A clinical close-up photograph of a skin lesion — 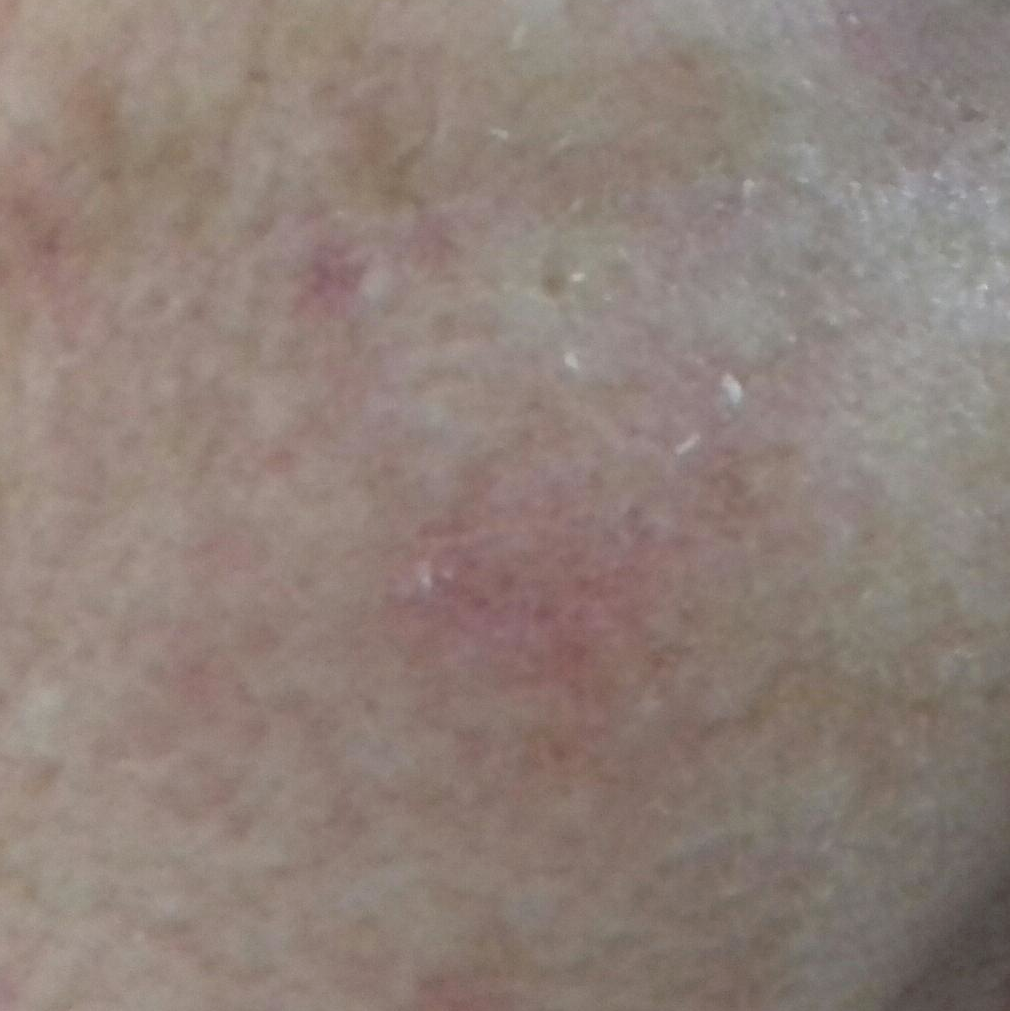<skin_lesion>
<lesion_location>the face</lesion_location>
<symptoms>
<present>itching</present>
<absent>bleeding</absent>
</symptoms>
<diagnosis>
<name>actinic keratosis</name>
<code>ACK</code>
<malignancy>indeterminate</malignancy>
<confirmation>clinical consensus</confirmation>
</diagnosis>
</skin_lesion>